The patient is a female aged 50–59 · the condition has been present for less than one week · located on the front of the torso and back of the torso · reported lesion symptoms include enlargement, burning and itching · the lesion is described as raised or bumpy · the patient considered this a rash · this is a close-up image — 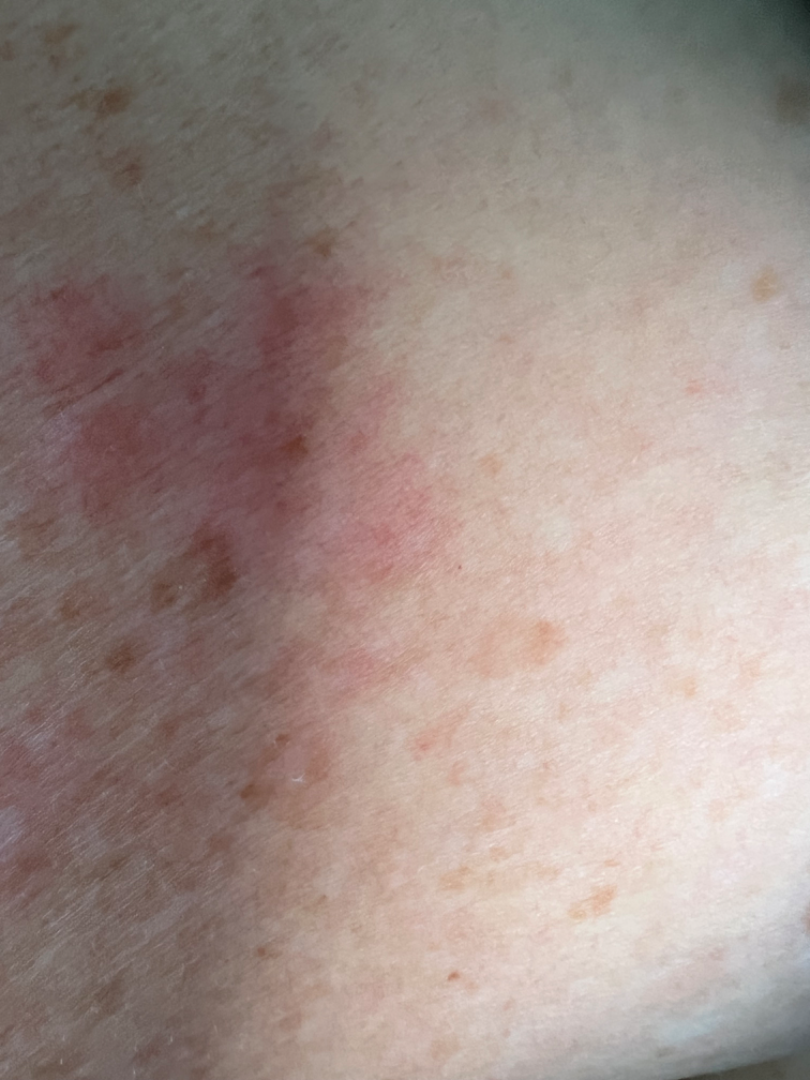Review: The image was not sufficient for the reviewer to characterize the skin condition.